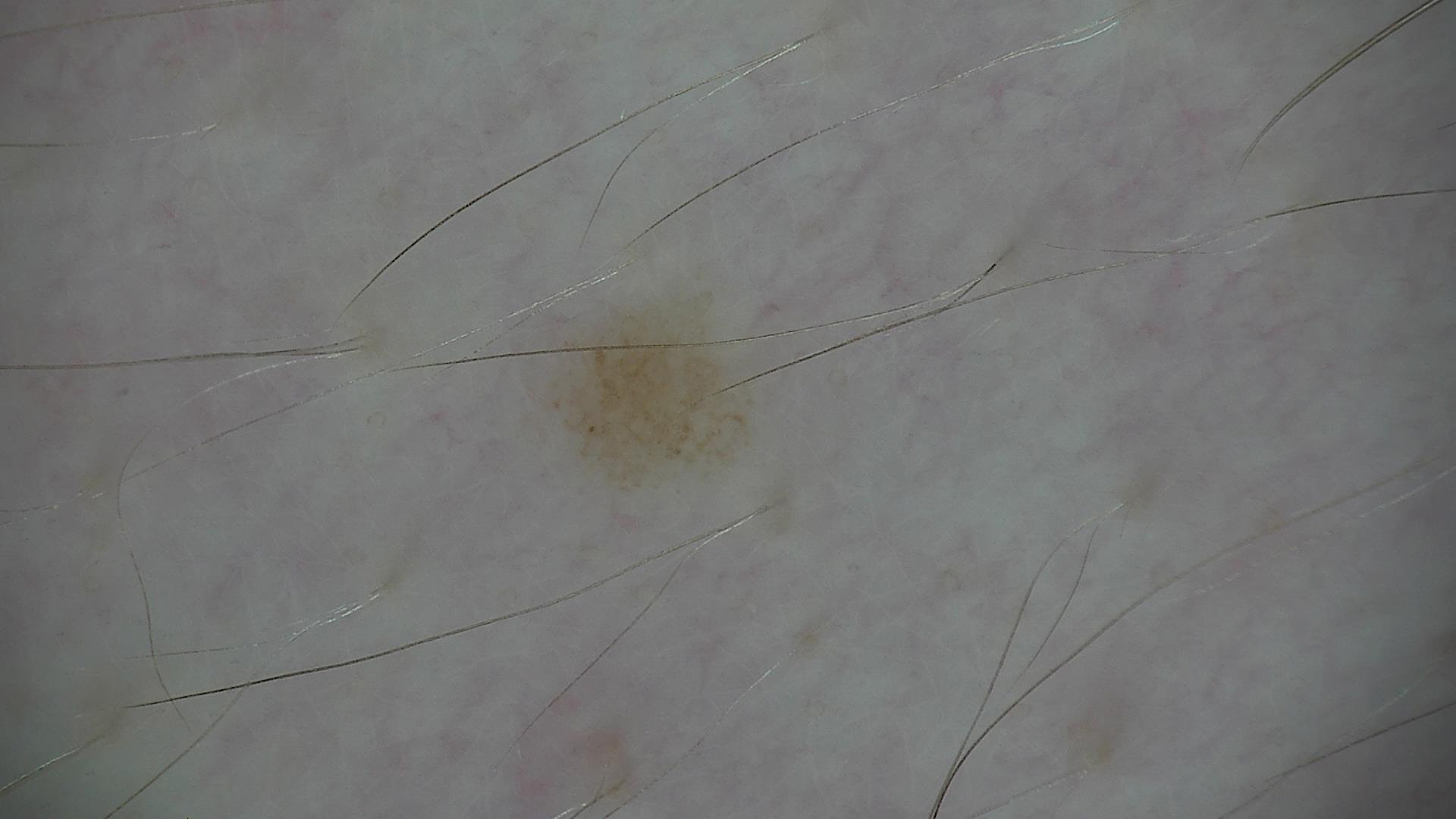A dermoscopy image of a single skin lesion. The diagnosis was a dysplastic junctional nevus.